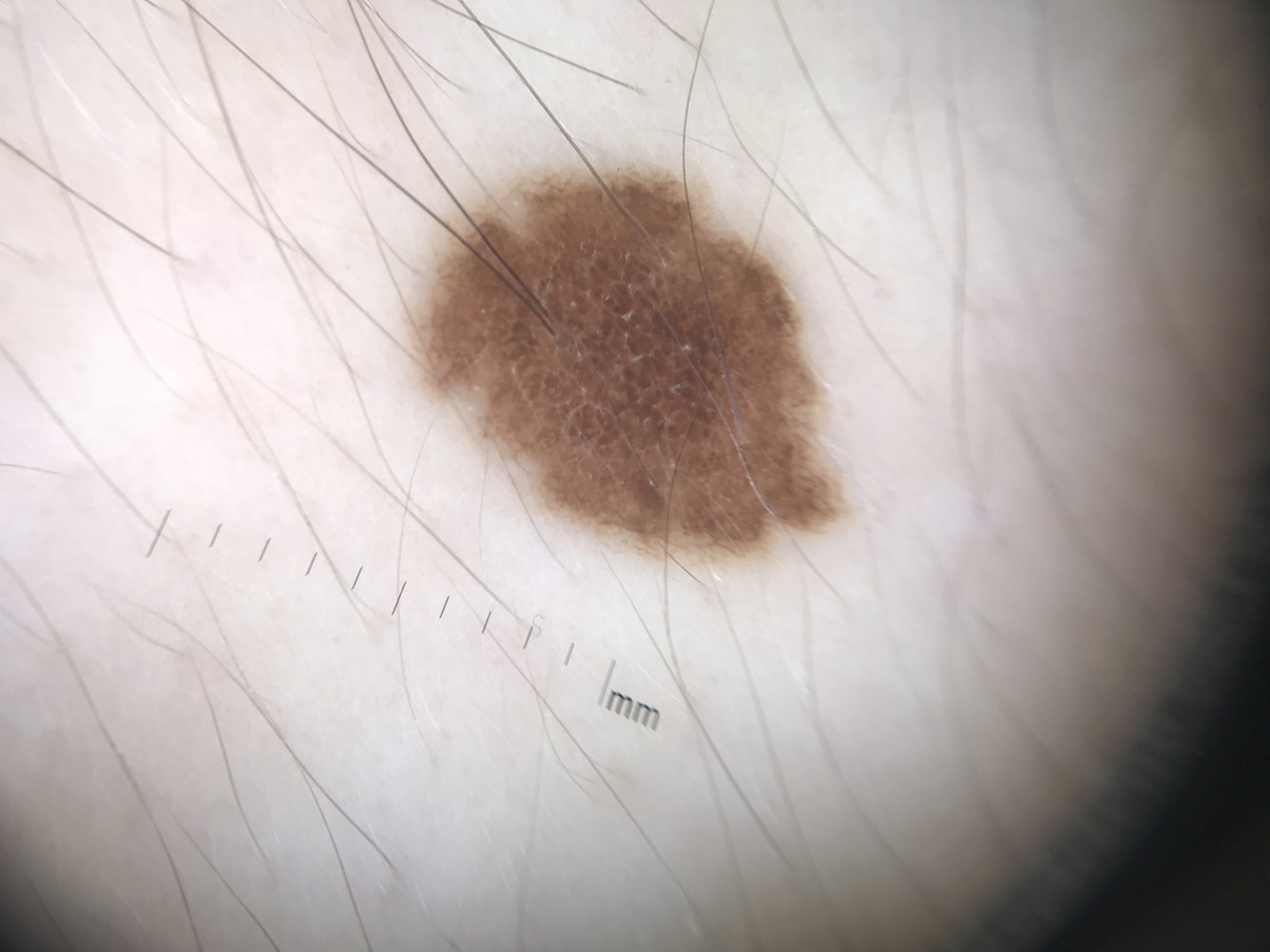modality = dermatoscopy; label = dysplastic junctional nevus (expert consensus).